A skin lesion imaged with a dermatoscope.
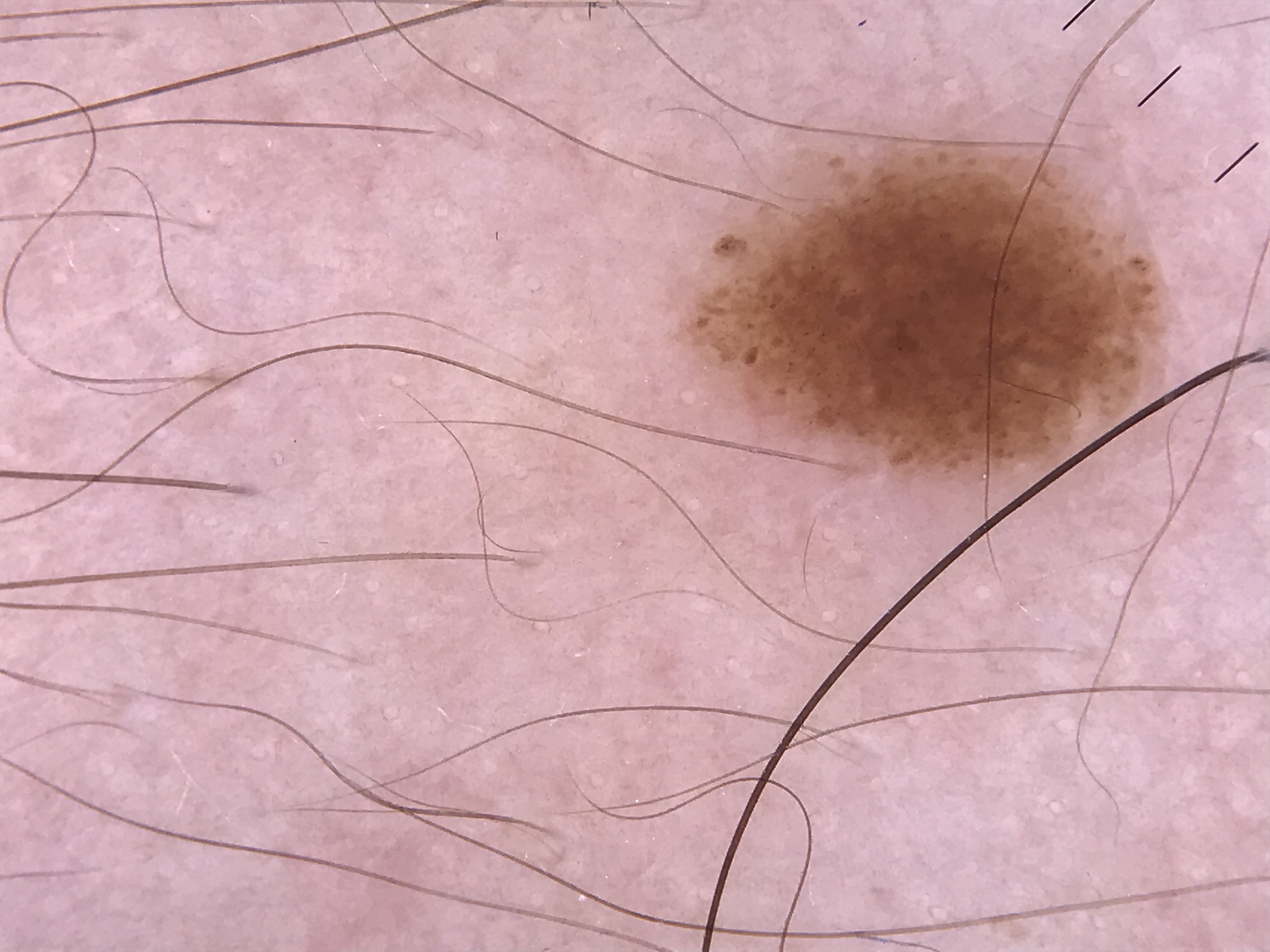class: dysplastic junctional nevus (expert consensus).